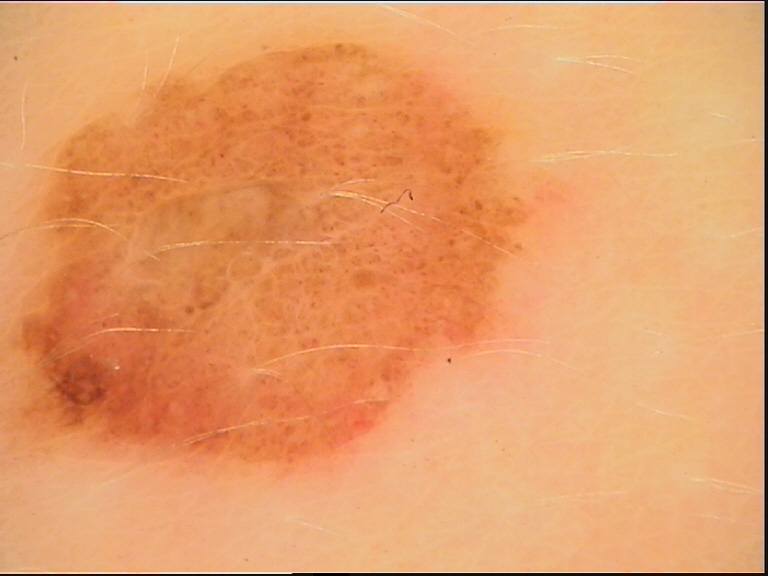Labeled as a compound nevus.